A dermoscopic close-up of a skin lesion:
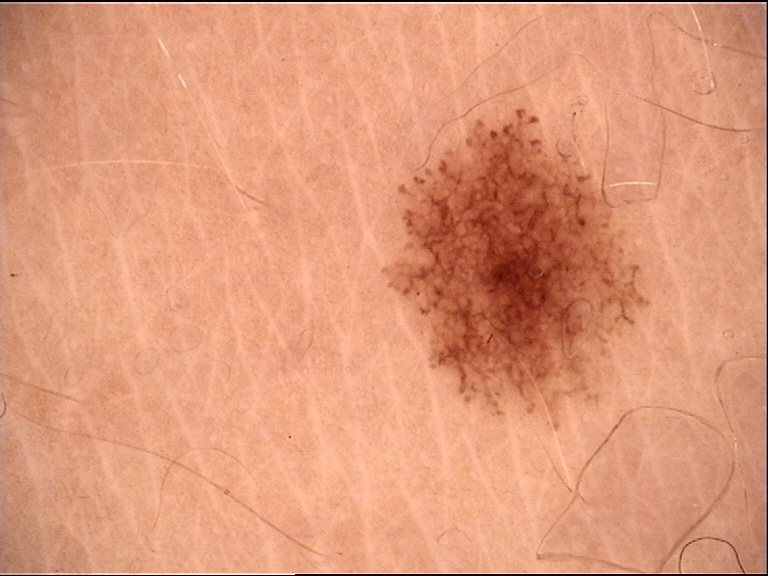Case:
* label · dysplastic junctional nevus (expert consensus)